The referring clinician suspected basal cell carcinoma; a female subject 60 years of age; a clinical photograph showing a skin lesion: 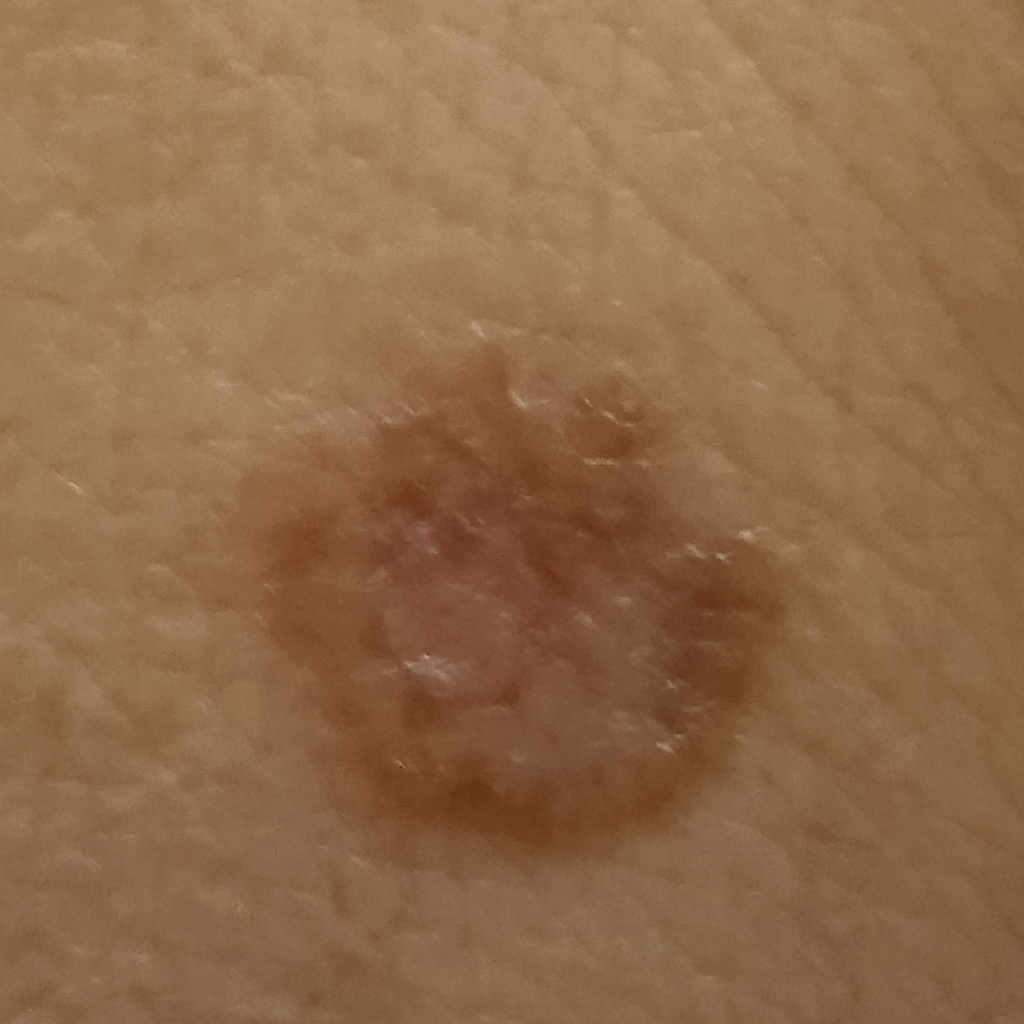Q: Where is the lesion?
A: the torso
Q: What was the diagnosis?
A: basal cell carcinoma (dermatologist consensus)